A clinical photograph showing a skin lesion.
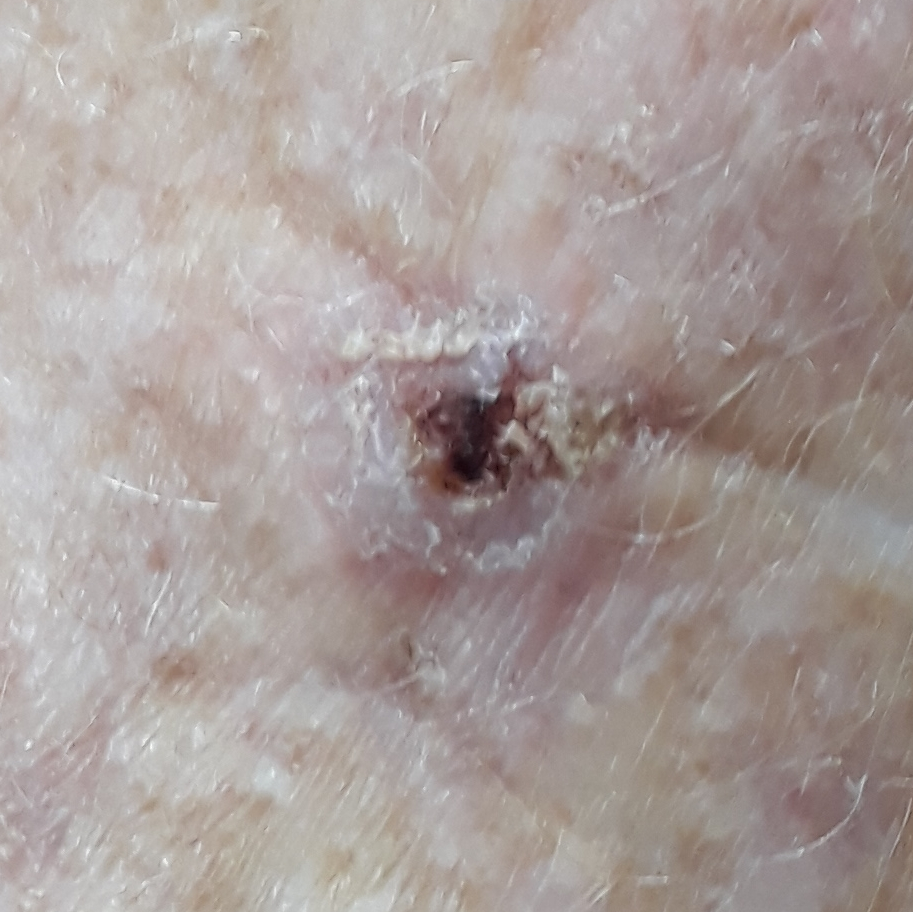Case summary:
Per patient report, the lesion itches, but does not hurt.
Diagnosis:
Confirmed on histopathology as an actinic keratosis.